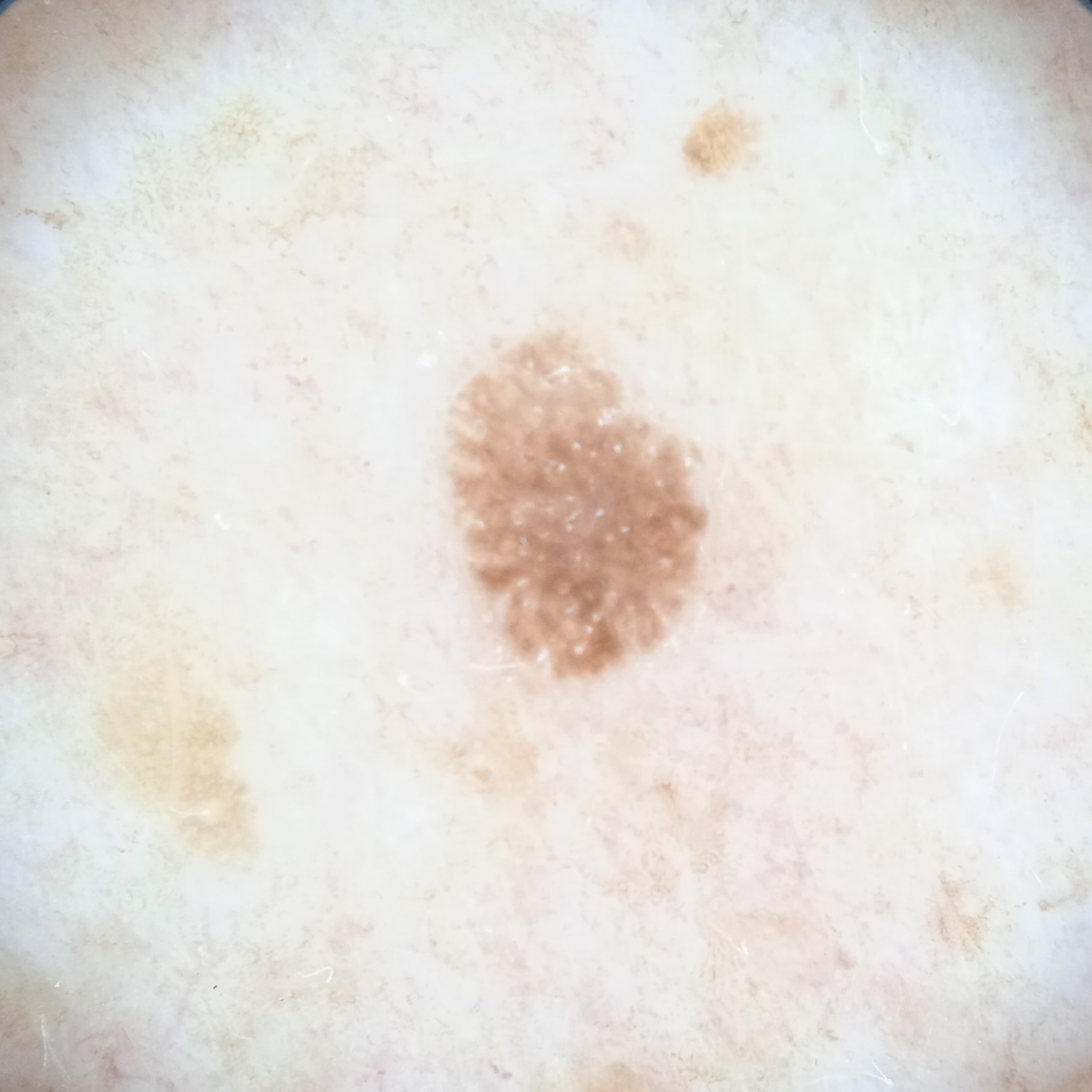{
  "referral": "research study (no referral diagnosis)",
  "image": "dermoscopic image",
  "patient": {
    "age": 62,
    "sex": "male"
  },
  "lesion_location": "the back",
  "lesion_size": {
    "diameter_mm": 4.3
  },
  "diagnosis": {
    "name": "seborrheic keratosis",
    "malignancy": "benign"
  }
}